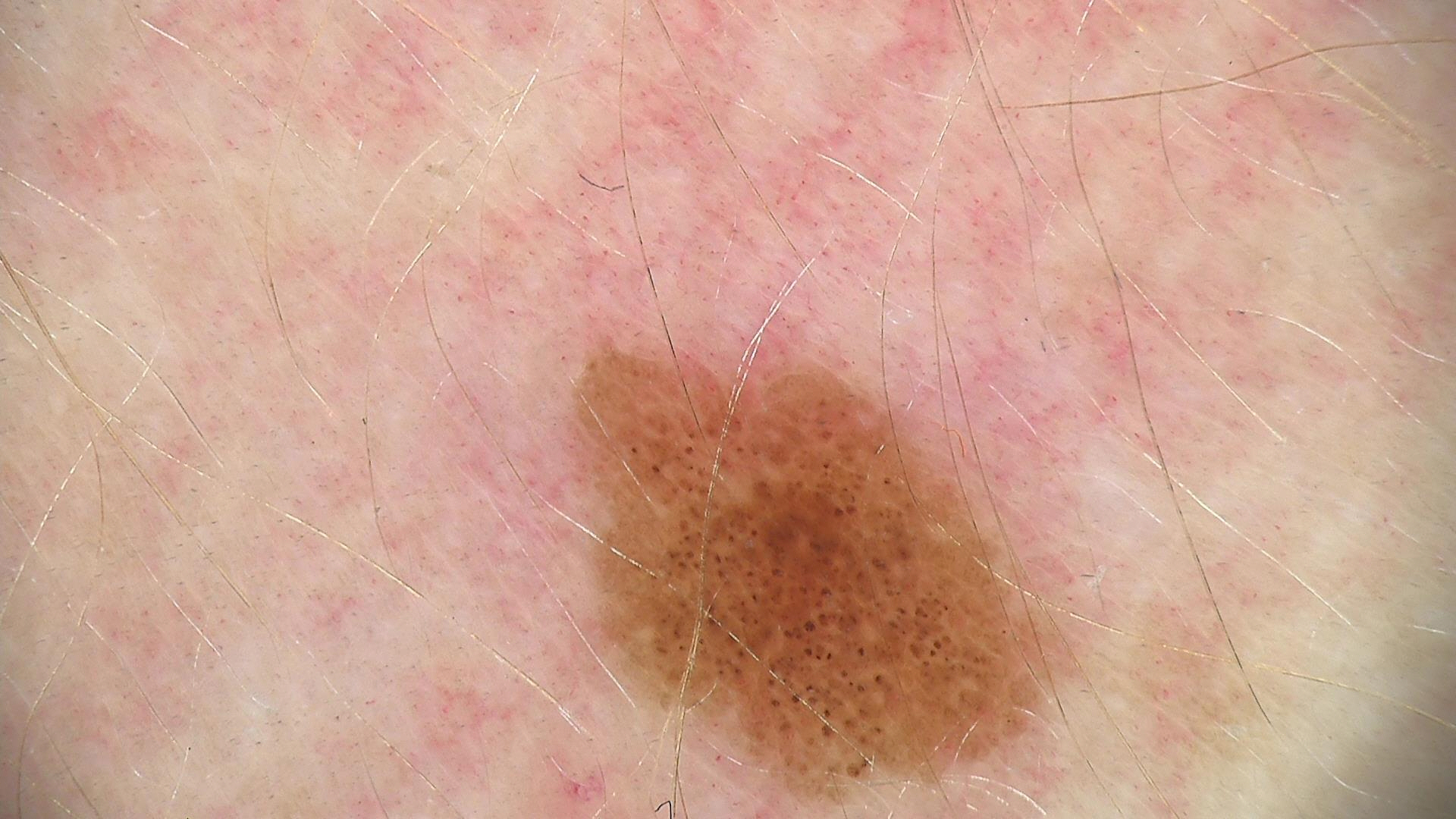A dermoscopy image of a single skin lesion. The architecture is that of a banal lesion. Diagnosed as a junctional nevus.